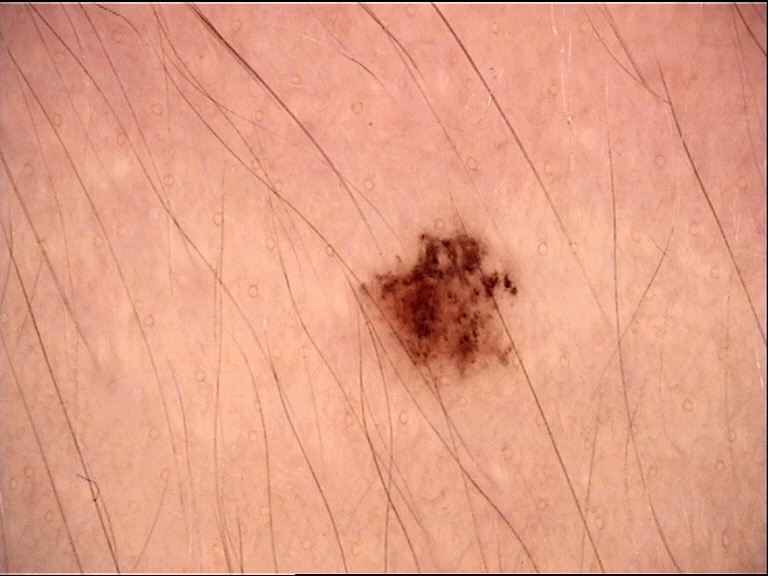A dermatoscopic image of a skin lesion. Consistent with a dysplastic junctional nevus.